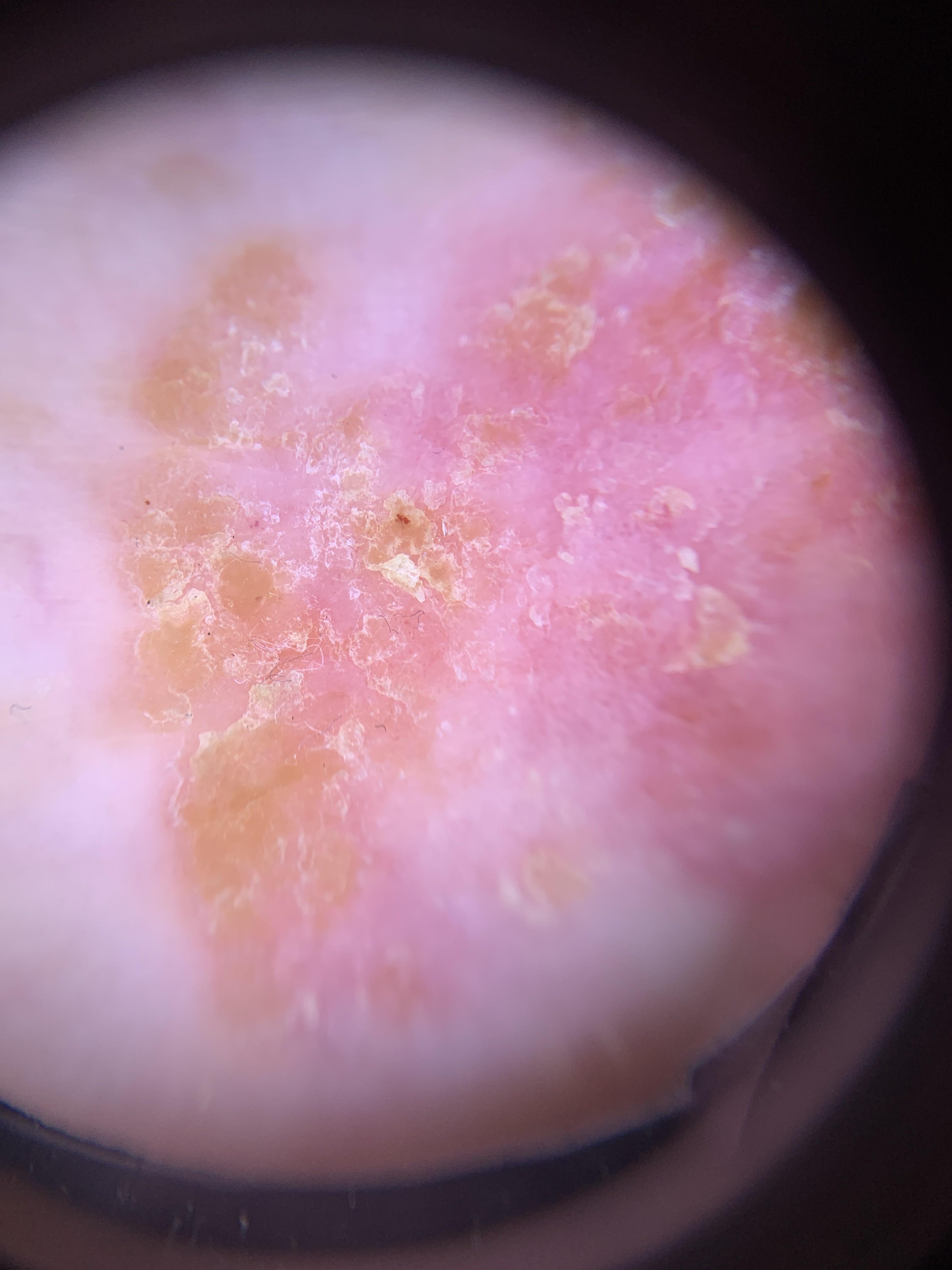A skin lesion imaged with contact-polarized dermoscopy.
A male patient aged approximately 85 or older.
The lesion involves a lower extremity.
Biopsy-confirmed as a squamous cell carcinoma.